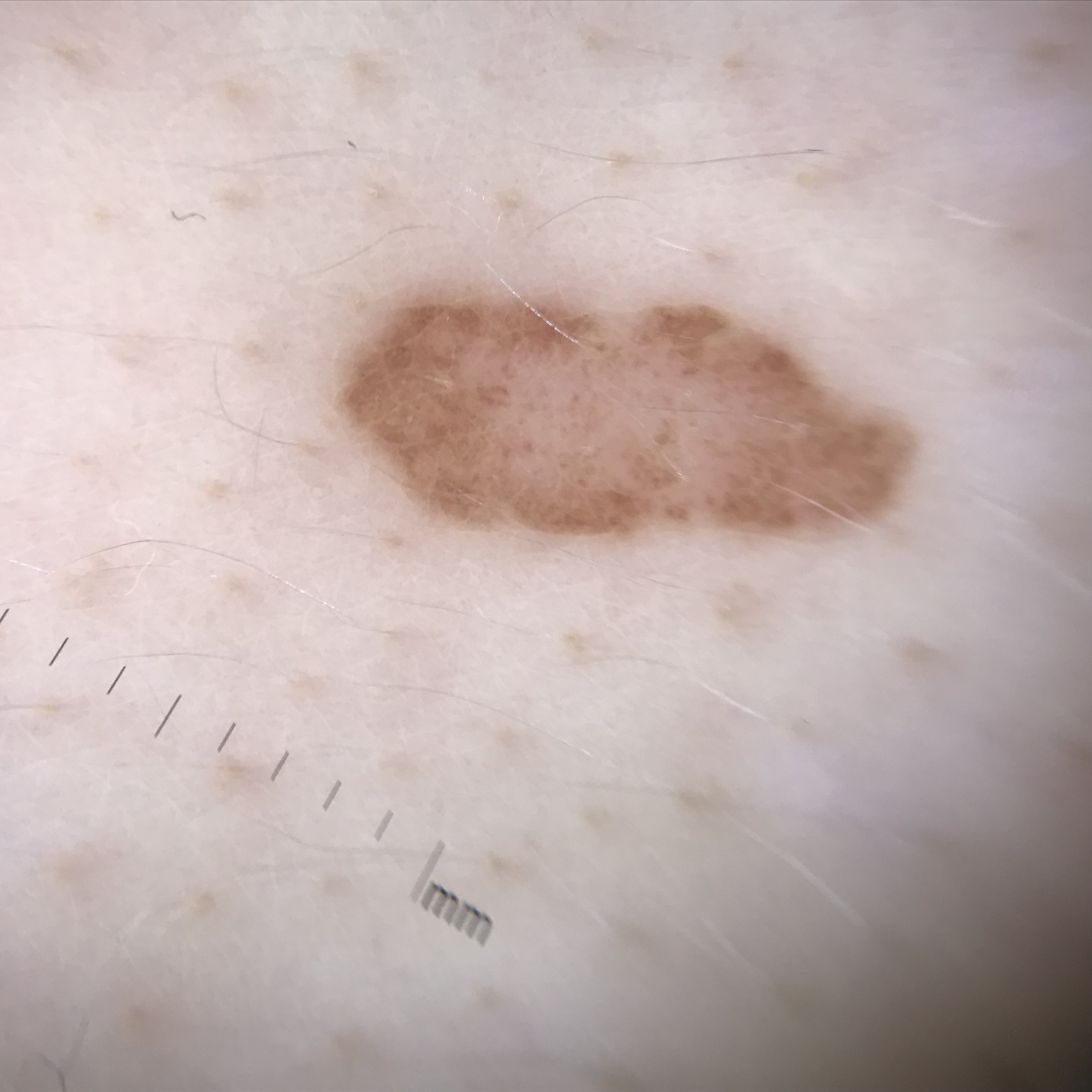diagnostic label — dysplastic compound nevus (expert consensus)